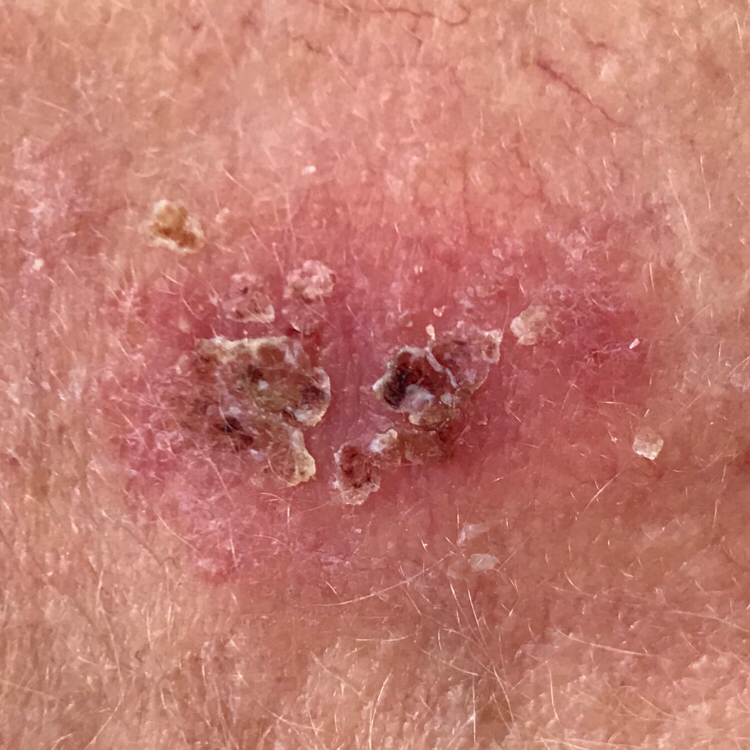image type — clinical photo
skin phototype — II
risk factors — prior malignancy (patient or family), prior skin cancer (patient or family), pesticide exposure
location — the face
size — 20 × 16 mm
diagnostic label — squamous cell carcinoma (biopsy-proven)